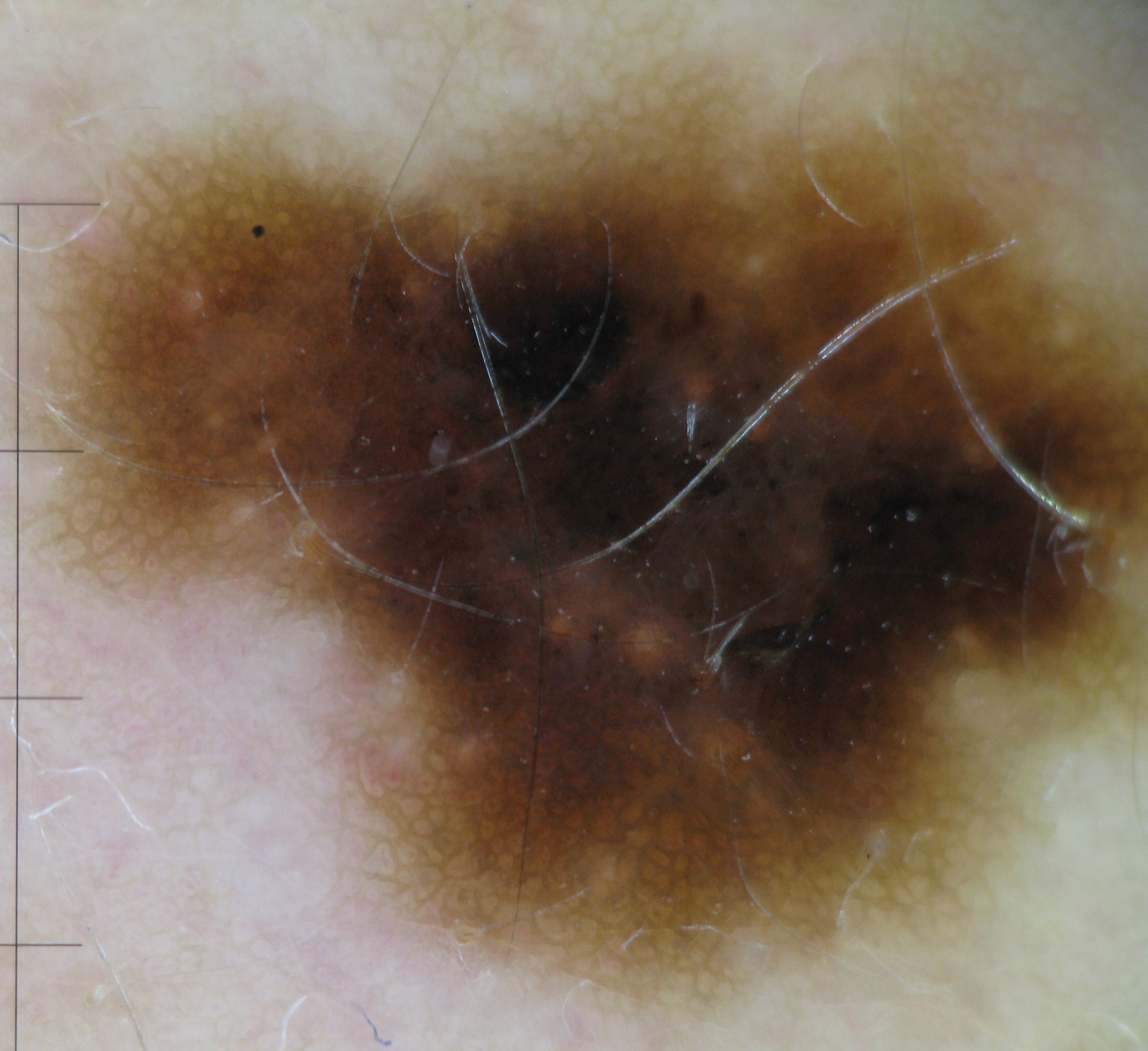| feature | finding |
|---|---|
| label | dysplastic compound nevus (expert consensus) |